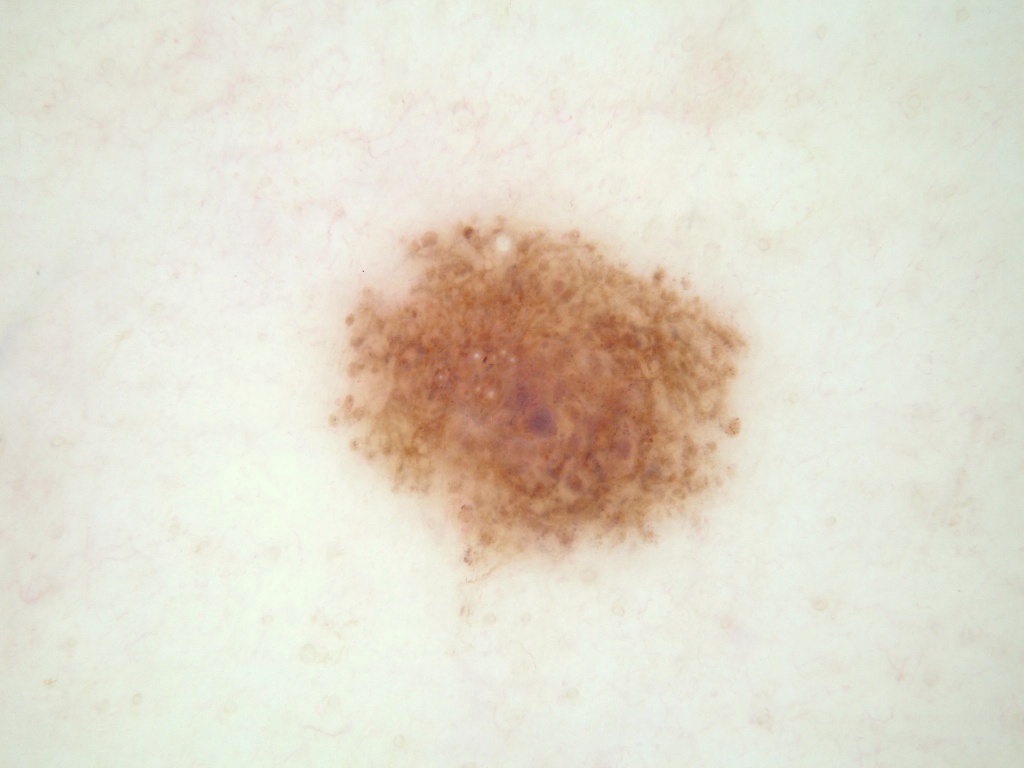patient = female, aged around 55
image = dermoscopy
lesion bbox = <box>327, 199, 757, 579</box>
lesion extent = ~15% of the field
dermoscopic features = milia-like cysts and globules; absent: streaks, pigment network, and negative network
assessment = a melanocytic nevus, a benign lesion